Close-up view · reported lesion symptoms include burning, pain and itching · the lesion involves the leg, arm and back of the hand · the patient reported no systemic symptoms · the condition has been present for more than five years · the subject is a female aged 40–49: 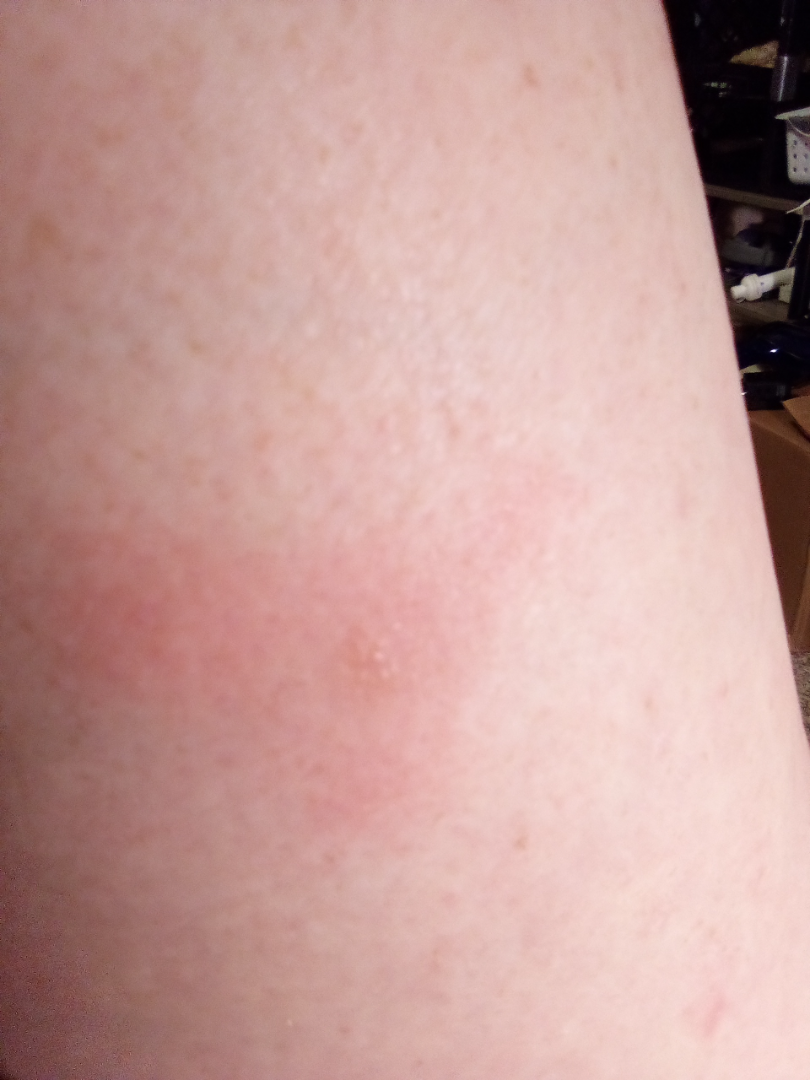Impression:
The leading consideration is Allergic Contact Dermatitis; also on the differential is Hypersensitivity.